The photo was captured at a distance; the arm is involved; the patient is 40–49, female: 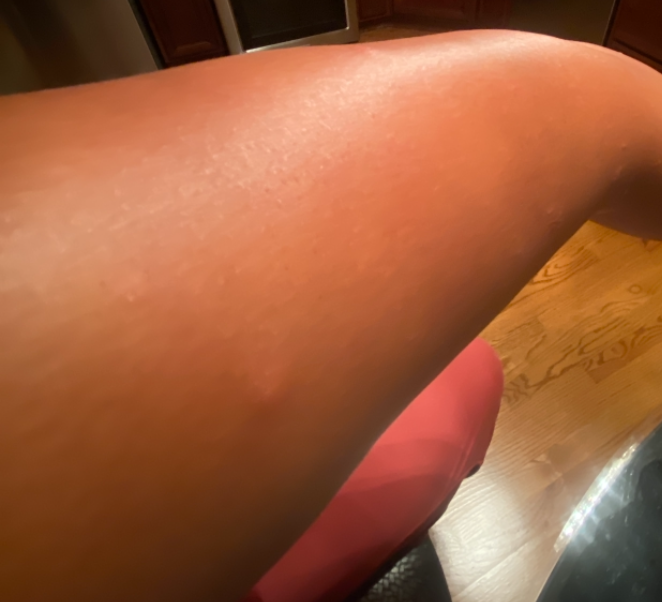The case was difficult to assess from the available photograph. Fitzpatrick skin type II. The patient reports enlargement, itching and burning. The patient reports associated fatigue. The lesion is described as raised or bumpy and rough or flaky. The patient considered this acne.